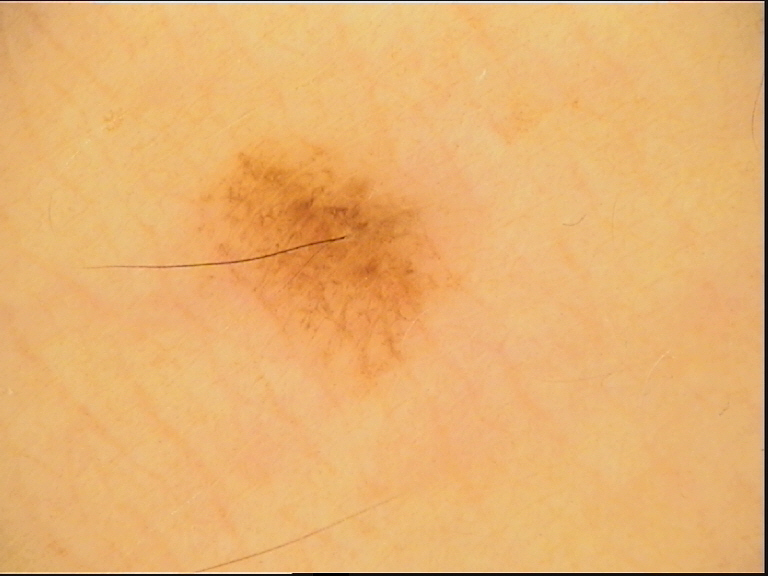assessment = dysplastic junctional nevus (expert consensus).